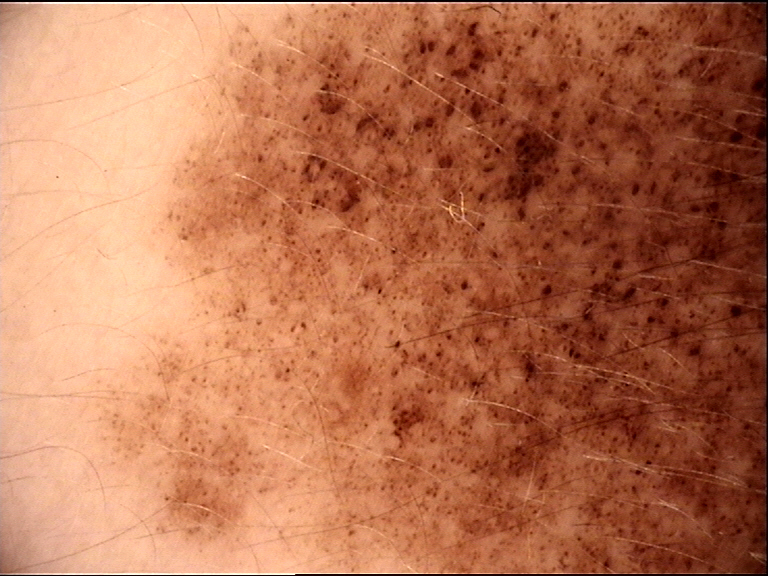This is a banal lesion.
The diagnostic label was a congenital compound nevus.